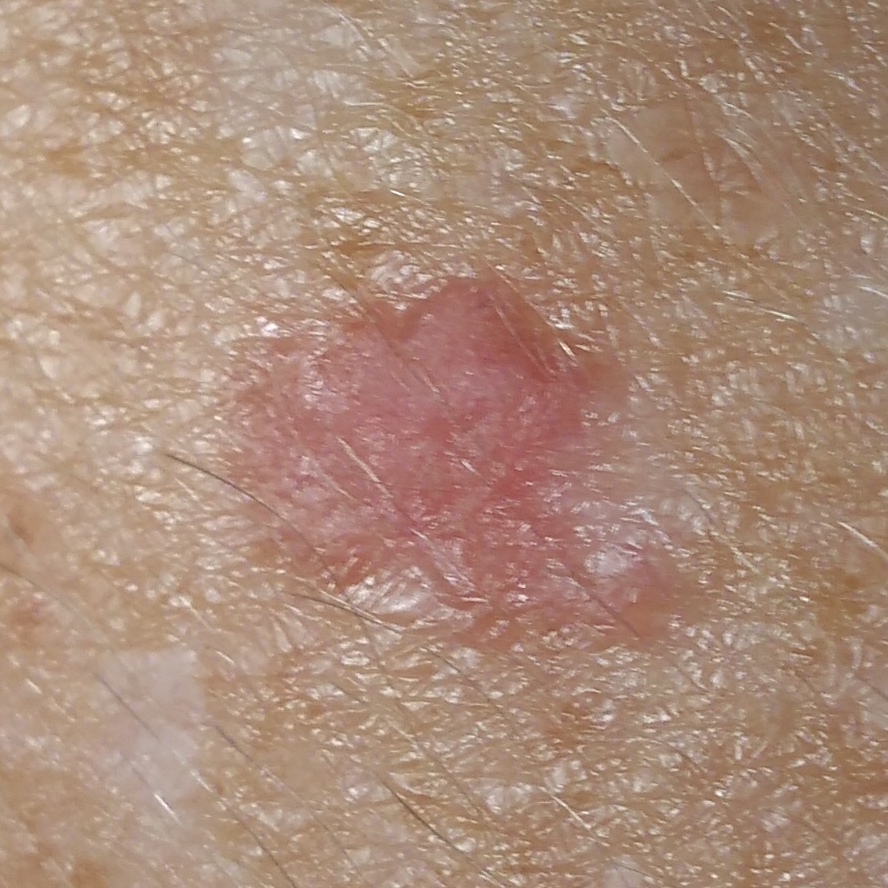Findings:
The lesion is on a forearm.
Diagnosis:
Histopathologically confirmed as a basal cell carcinoma.